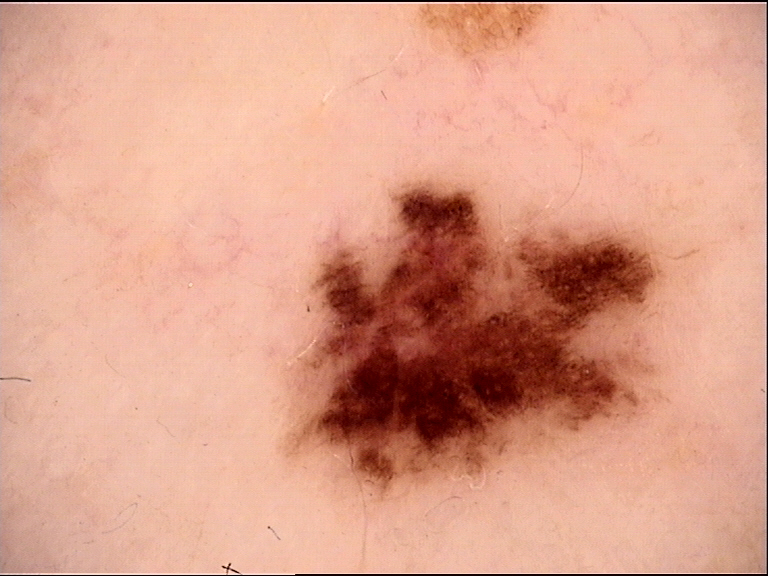Diagnosed as a dysplastic junctional nevus.